Close-up view; the lesion involves the leg; the subject is 70–79, female — 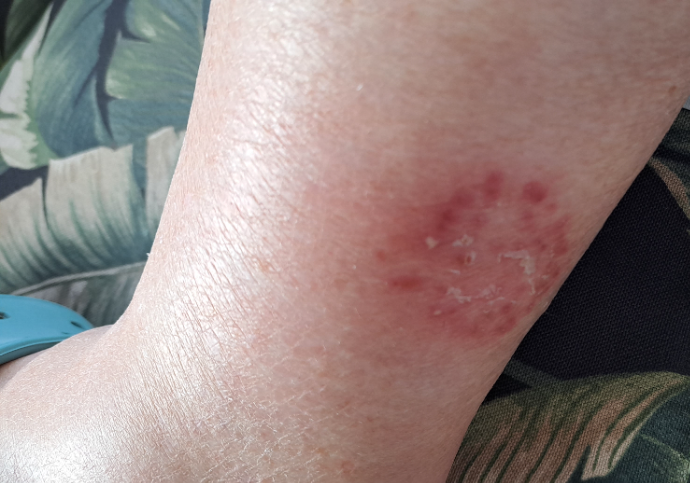History:
The patient considered this a rash. Present for one to four weeks. Fitzpatrick phototype II. Reported lesion symptoms include bothersome appearance.
Impression:
On remote dermatologist review, consistent with Eczema.